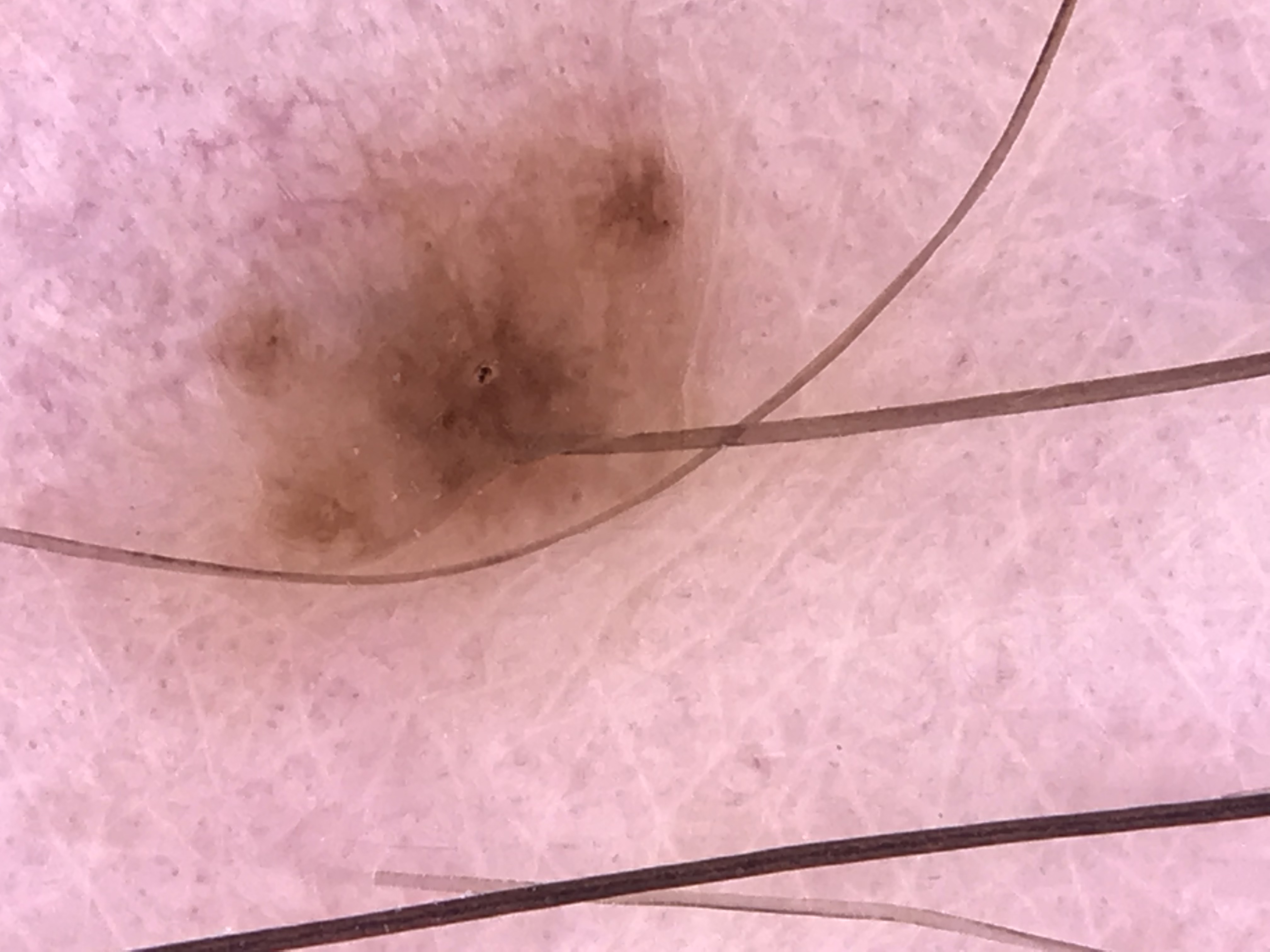<dermoscopy>
  <image>dermatoscopy</image>
  <lesion_type>
    <main_class>banal</main_class>
    <pattern>compound</pattern>
  </lesion_type>
  <diagnosis>
    <name>compound nevus</name>
    <code>cb</code>
    <malignancy>benign</malignancy>
    <super_class>melanocytic</super_class>
    <confirmation>expert consensus</confirmation>
  </diagnosis>
</dermoscopy>